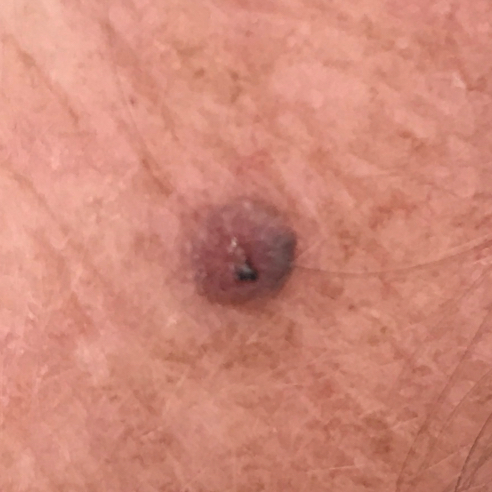History notes prior skin cancer (patient or family).
The patient is Fitzpatrick phototype II.
A female patient in their 60s.
A clinical close-up photograph of a skin lesion.
The lesion is located on the face.
The lesion is roughly 5 by 5 mm.
The patient reports that the lesion has bled, itches, and has grown, but is not elevated.
The biopsy diagnosis was a seborrheic keratosis.